A close-up photograph · male contributor, age 50–59 · the affected area is the back of the torso:
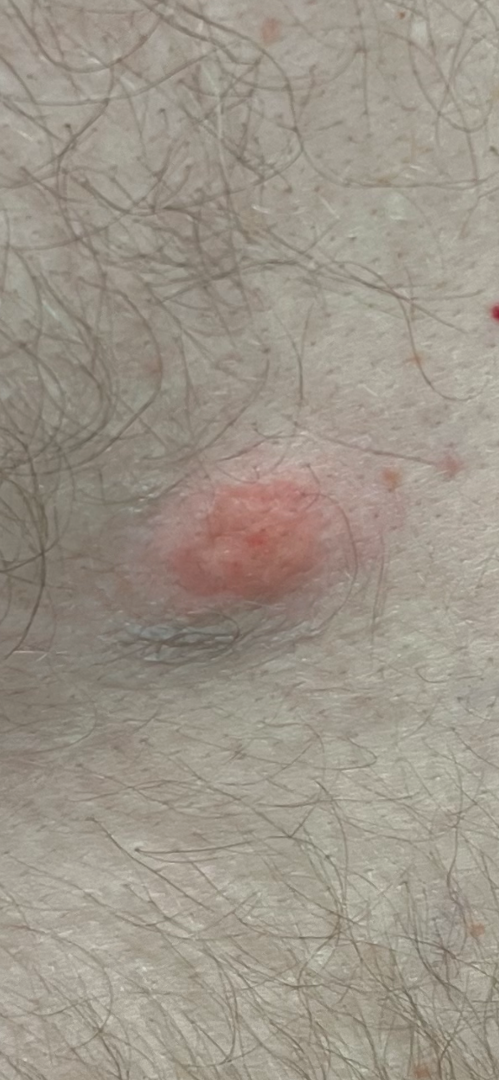Notes:
– assessment: indeterminate from the photograph
– associated systemic symptoms: none reported
– patient's own categorization: a rash
– lesion texture: raised or bumpy
– symptom duration: about one day